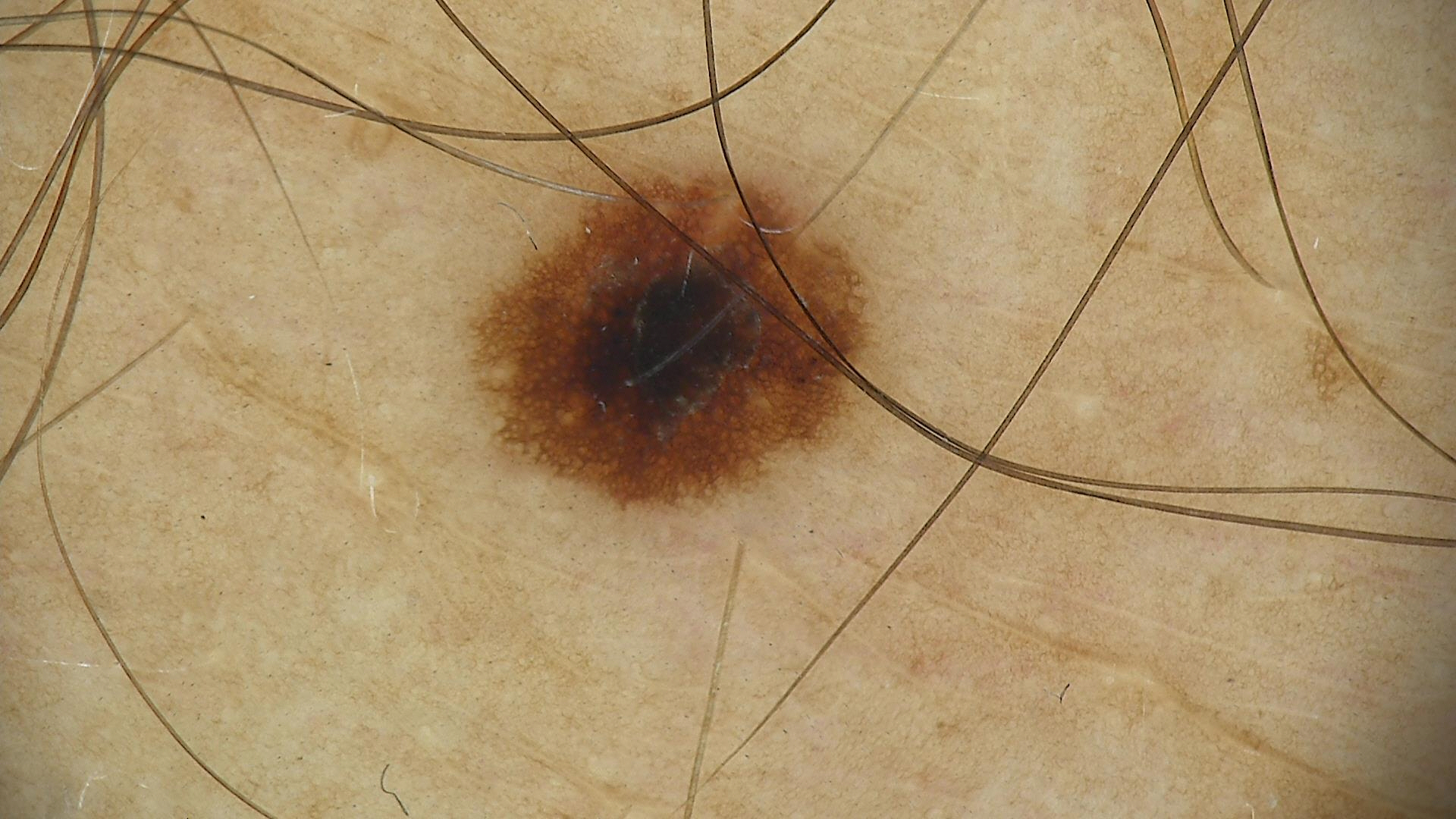<case>
<diagnosis>
<name>dysplastic junctional nevus</name>
<code>jd</code>
<malignancy>benign</malignancy>
<super_class>melanocytic</super_class>
<confirmation>expert consensus</confirmation>
</diagnosis>
</case>